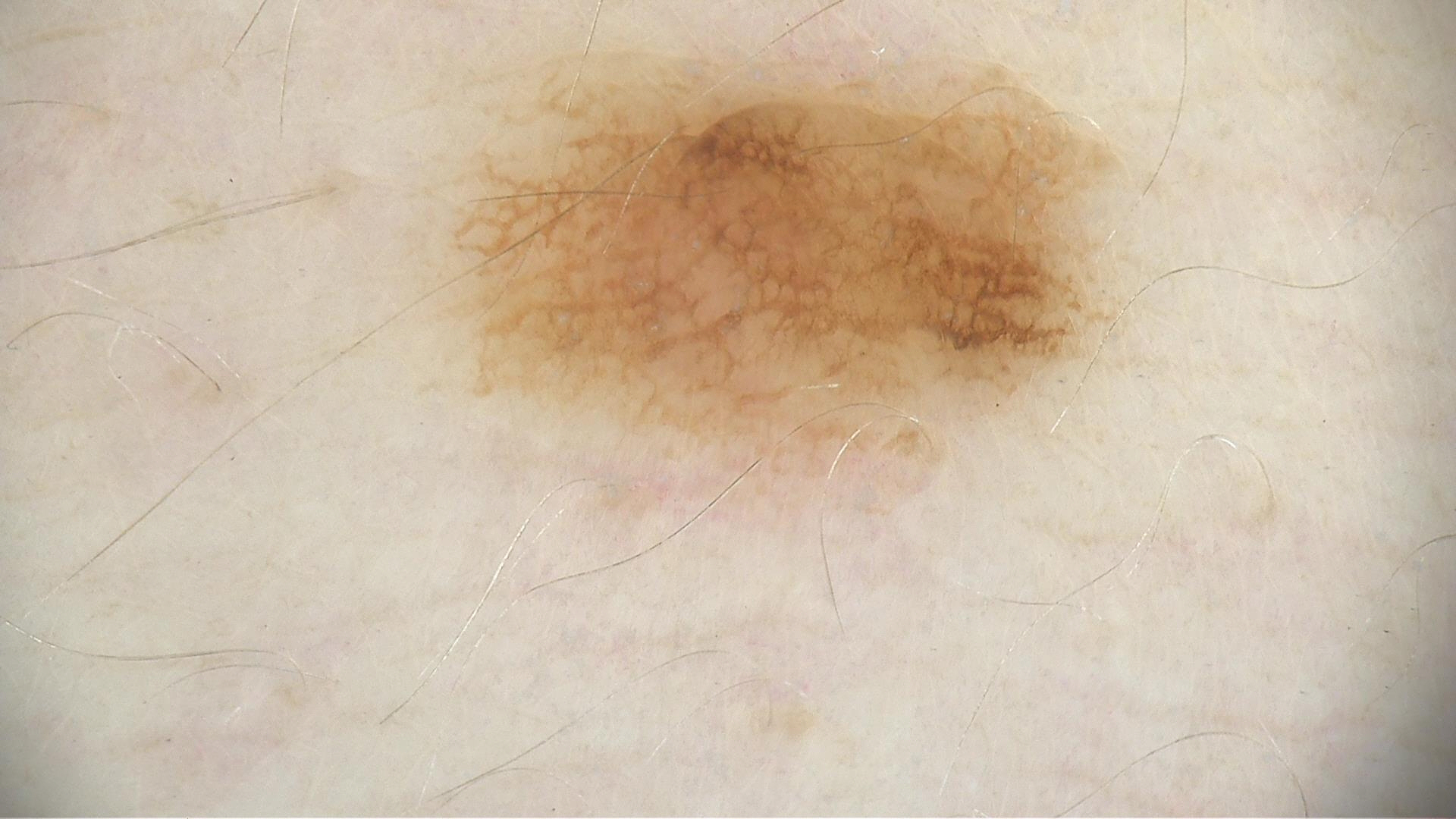Impression: The diagnostic label was a benign lesion — a dysplastic junctional nevus.